A dermoscopic photograph of a skin lesion.
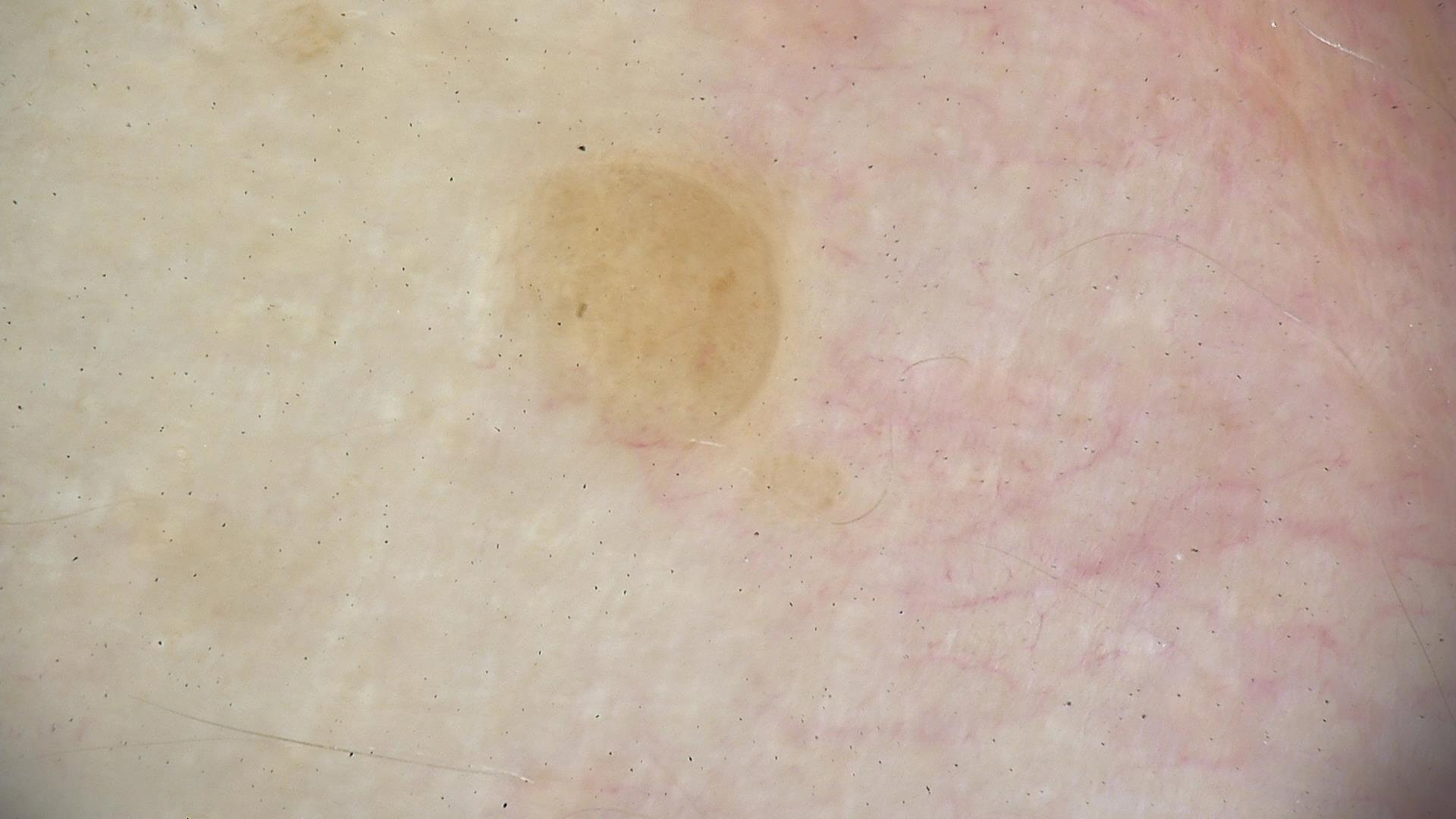Labeled as a banal lesion — a dermal nevus.